This is a close-up image. The contributor is 30–39, male. The back of the torso is involved. The contributor notes the condition has been present for about one day.
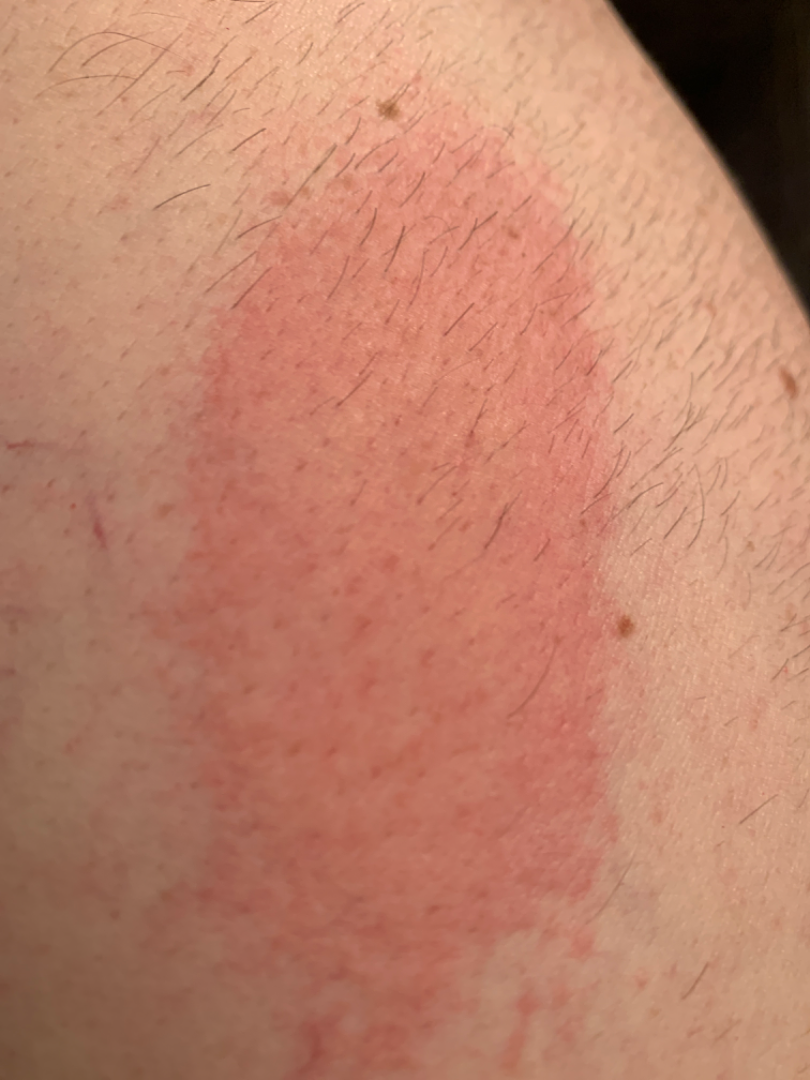<report>
  <differential>
    <tied_lead>Urticaria, Eczema</tied_lead>
    <unlikely>Drug Rash</unlikely>
  </differential>
</report>